A dermoscopy image of a single skin lesion.
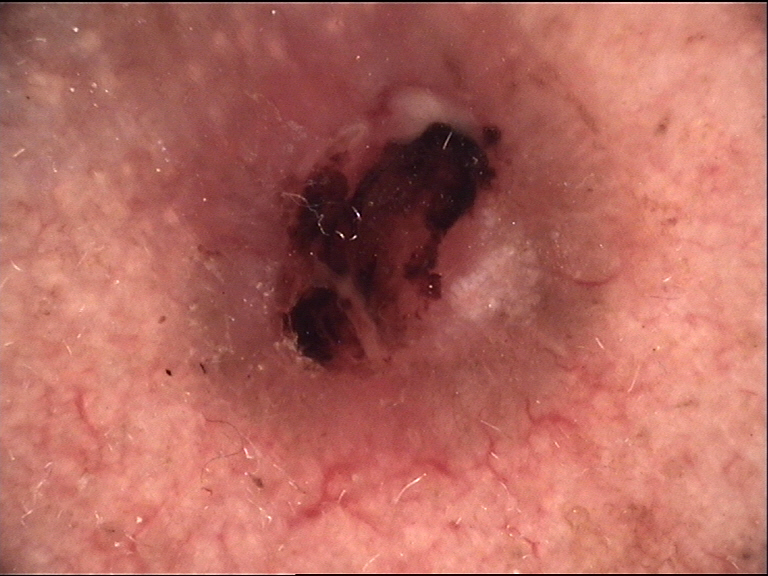Diagnosis:
Histopathology confirmed a skin cancer — a basal cell carcinoma.